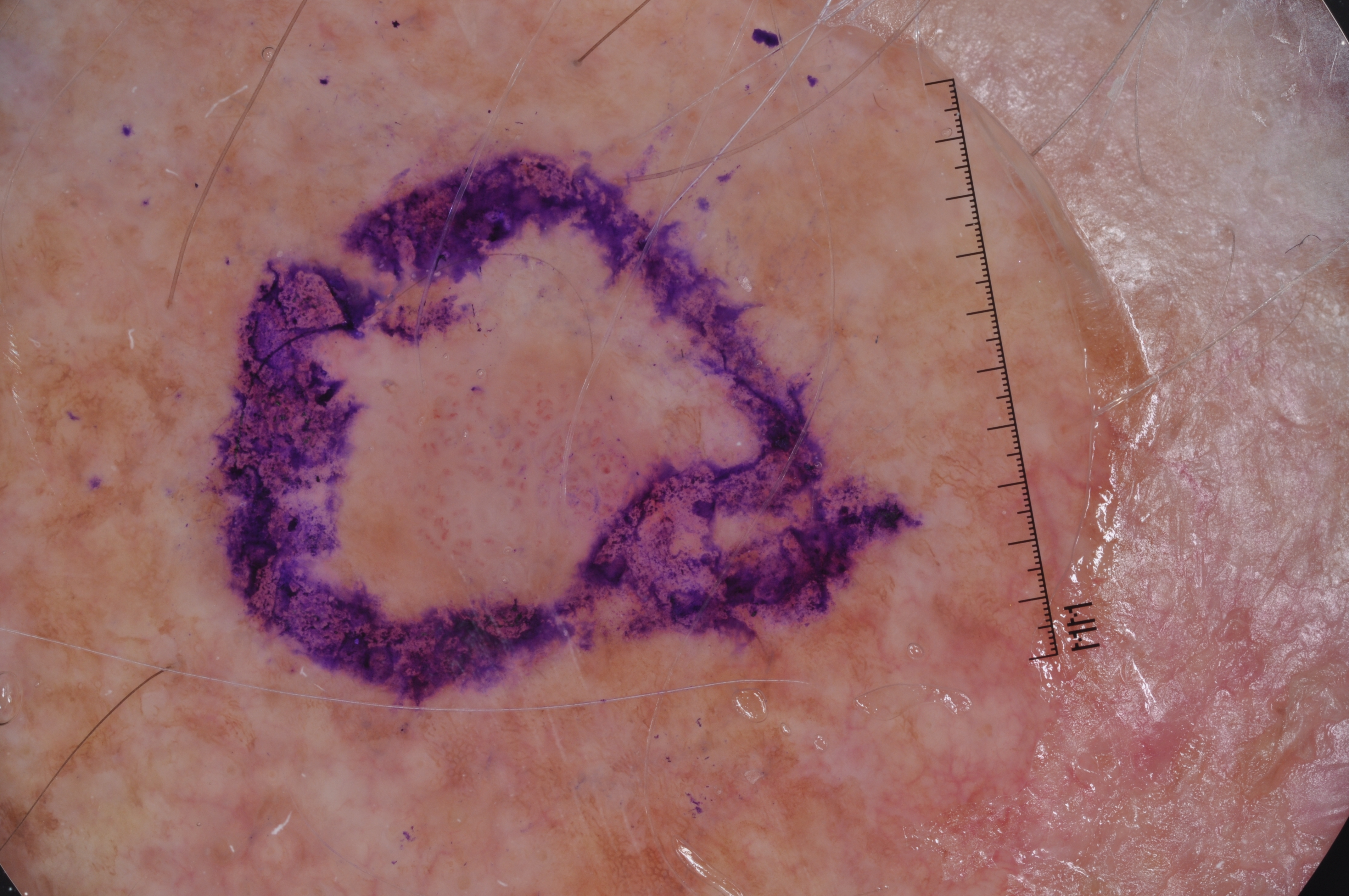Dermoscopy of a skin lesion.
A male patient, roughly 85 years of age or older.
The dermoscopic pattern shows no negative network, streaks, milia-like cysts, or pigment network.
In (x1, y1, x2, y2) order, the lesion's extent is 359, 311, 707, 630.
Consistent with a seborrheic keratosis, a benign skin lesion.